A dermoscopy image of a skin lesion. Imaged for a research study, with no referral diagnosis recorded. A male subject 72 years old. The patient says their skin tans without first burning.
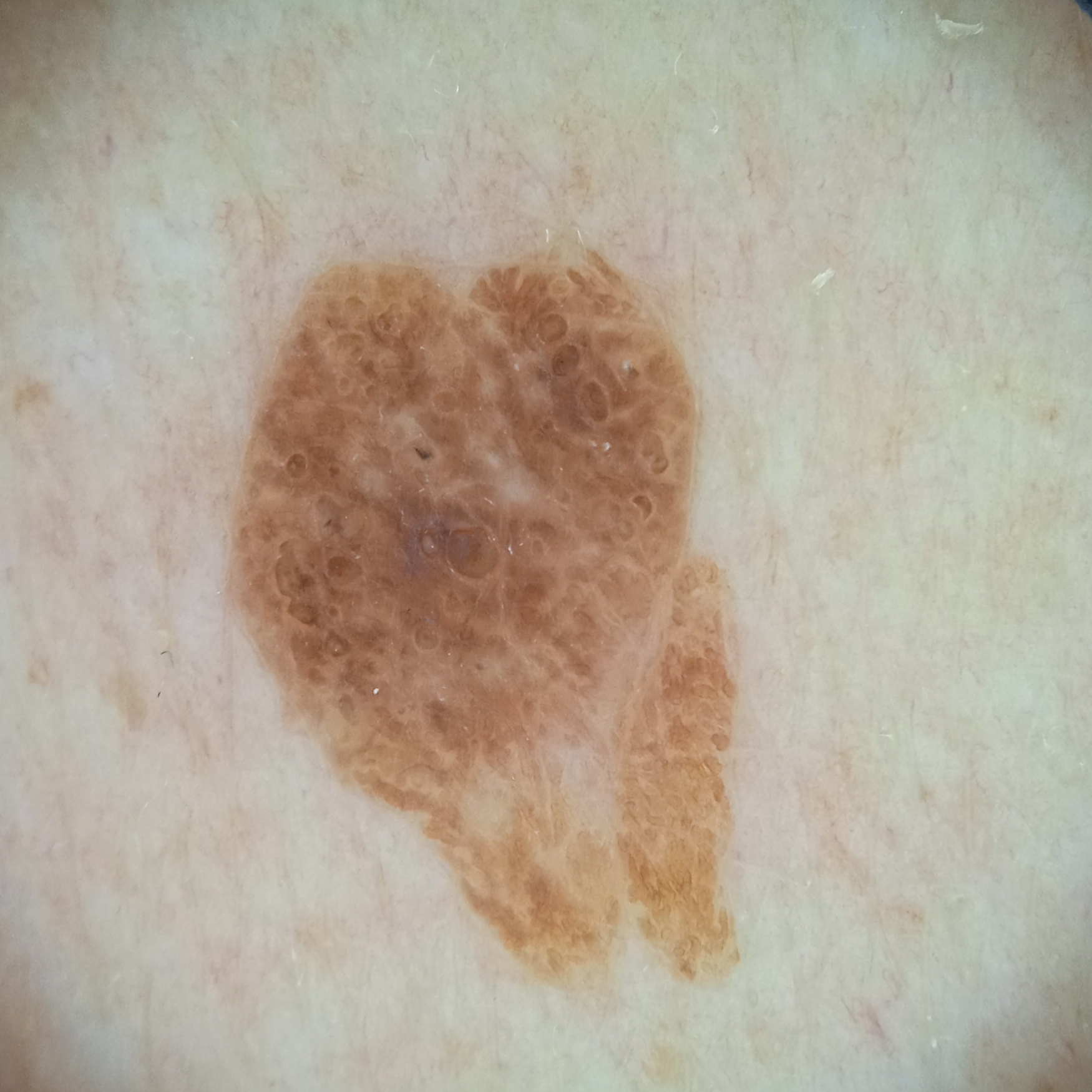Findings:
Located on the back. Measuring roughly 9.6 mm.
Conclusion:
The consensus diagnosis for this lesion was a seborrheic keratosis.